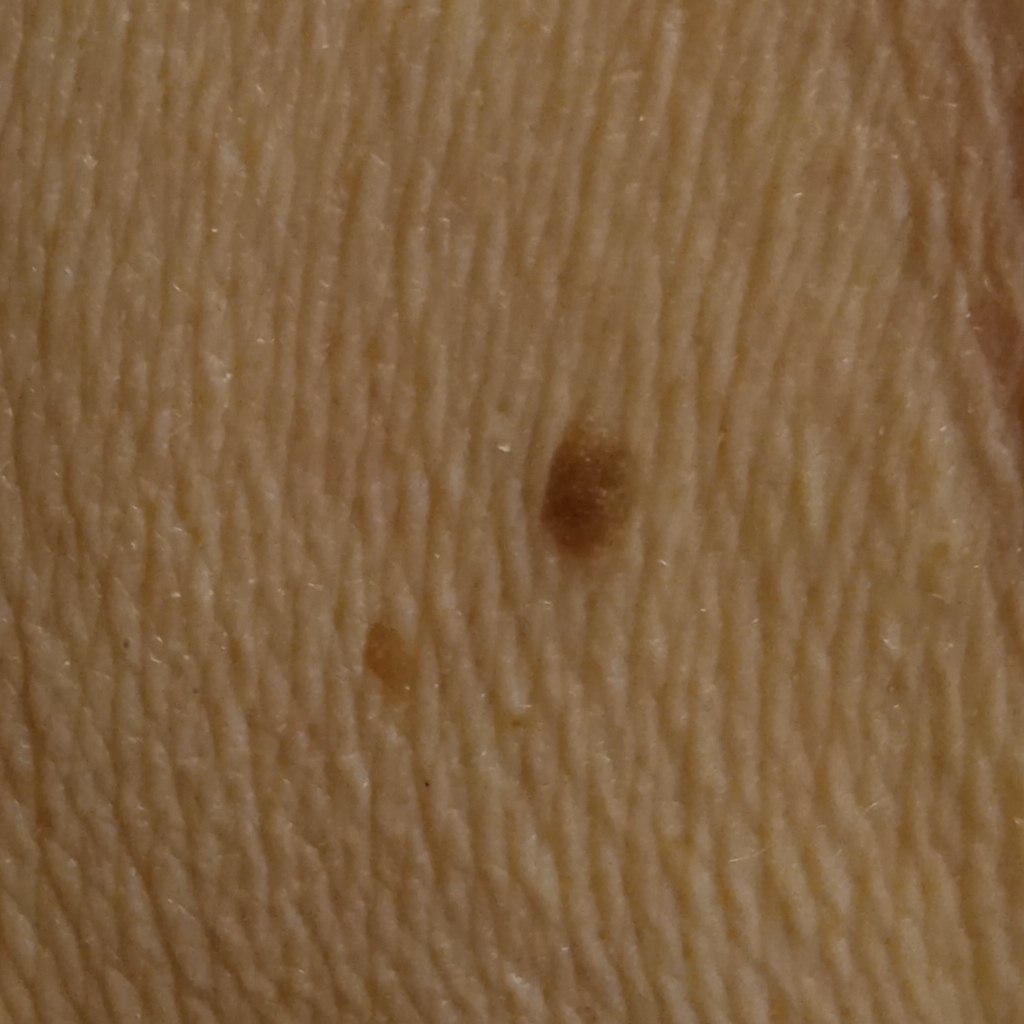Acquired for a research image collection, with no referral diagnosis. The patient reports no sunbed use. A clinical photograph of a skin lesion. The patient describes having few moles overall. A female subject age 73. The patient says their skin reddens with sun exposure. Located on the back. The lesion measures approximately 6 mm. The consensus diagnosis for this lesion was a seborrheic keratosis.